The patient is Fitzpatrick phototype II · a contact-polarized dermoscopy image of a skin lesion · a female subject aged 33 to 37.
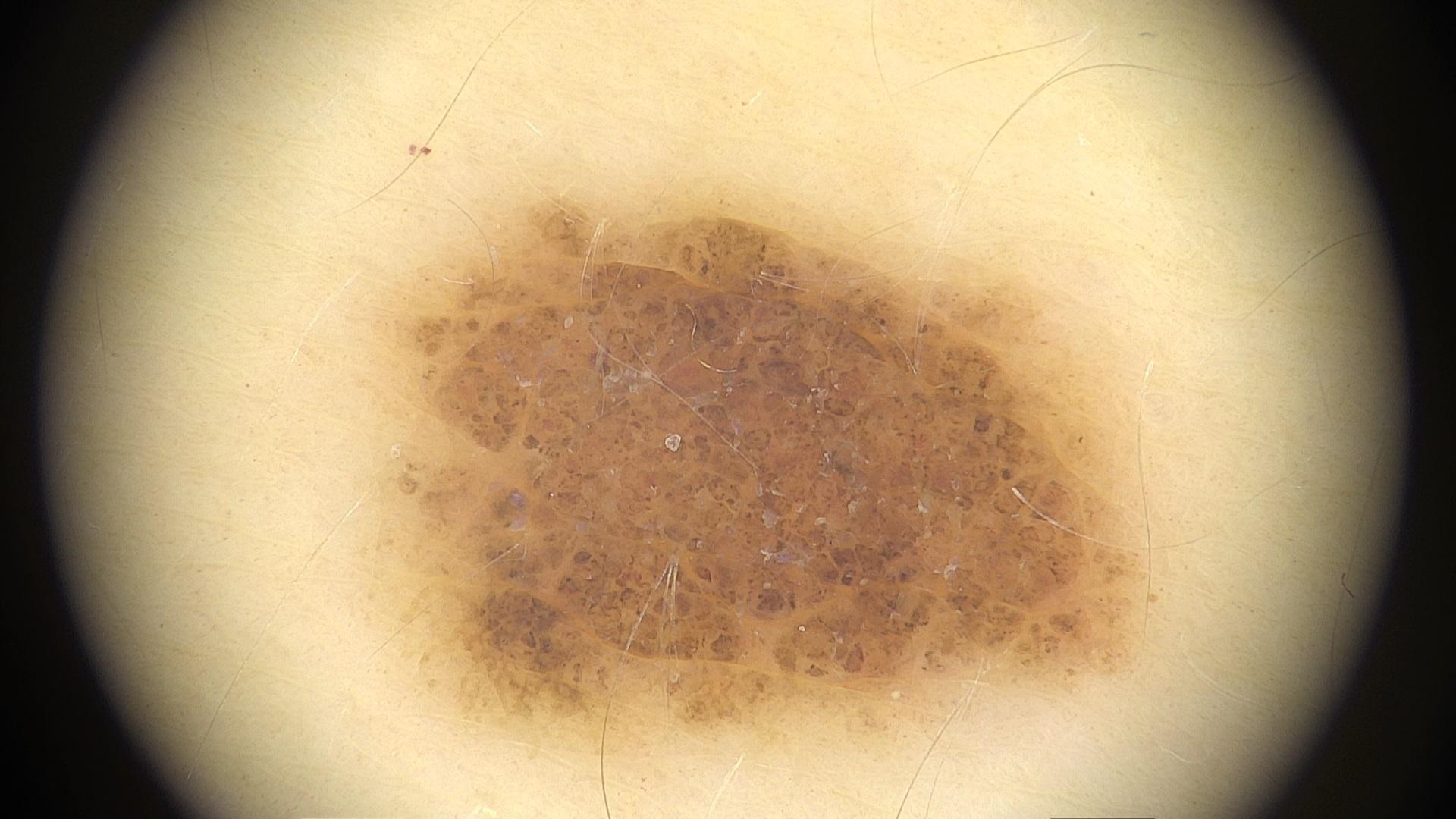- anatomic site · the trunk
- assessment · Nevus